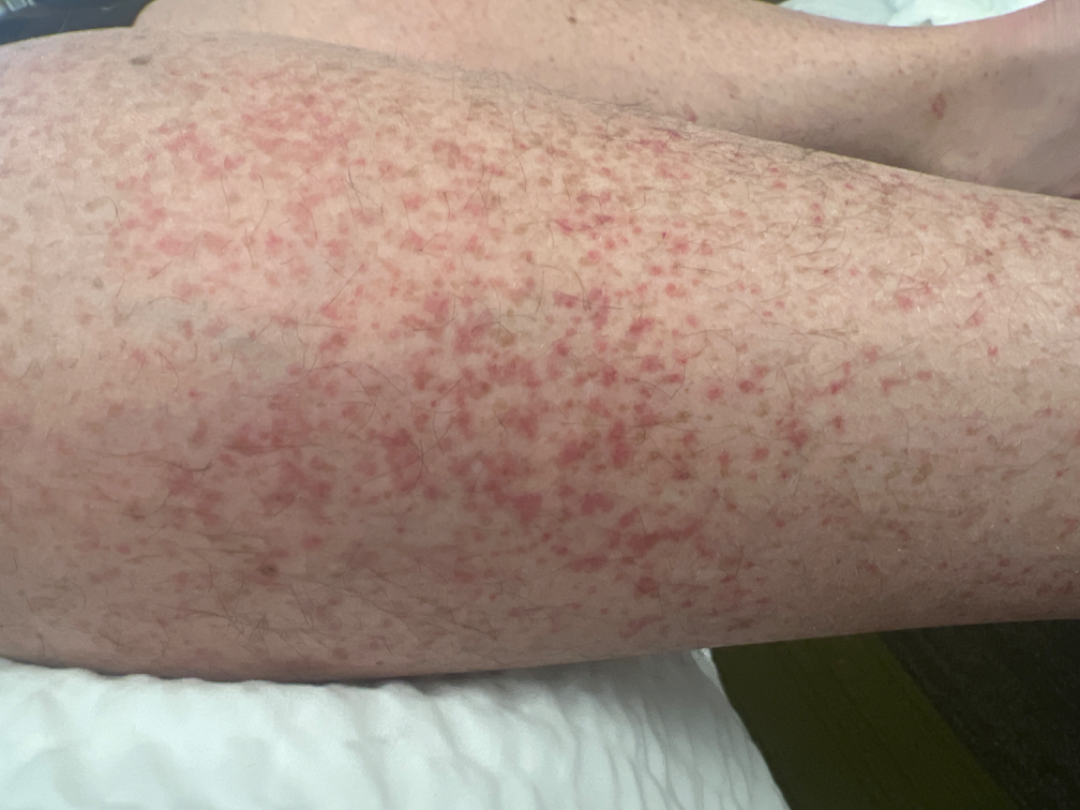On remote review of the image, the impression is Leukocytoclastic Vasculitis.